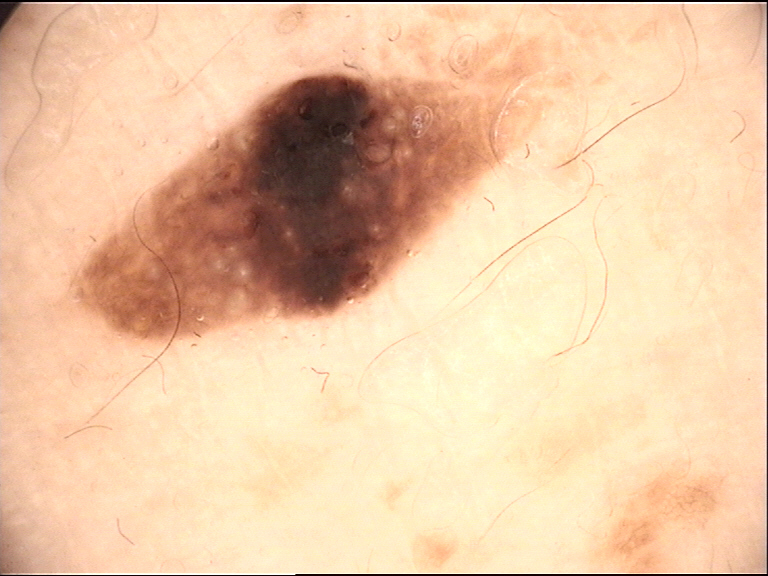The morphology is that of a keratinocytic lesion. Labeled as a benign lesion — a seborrheic keratosis.